A dermoscopic close-up of a skin lesion: 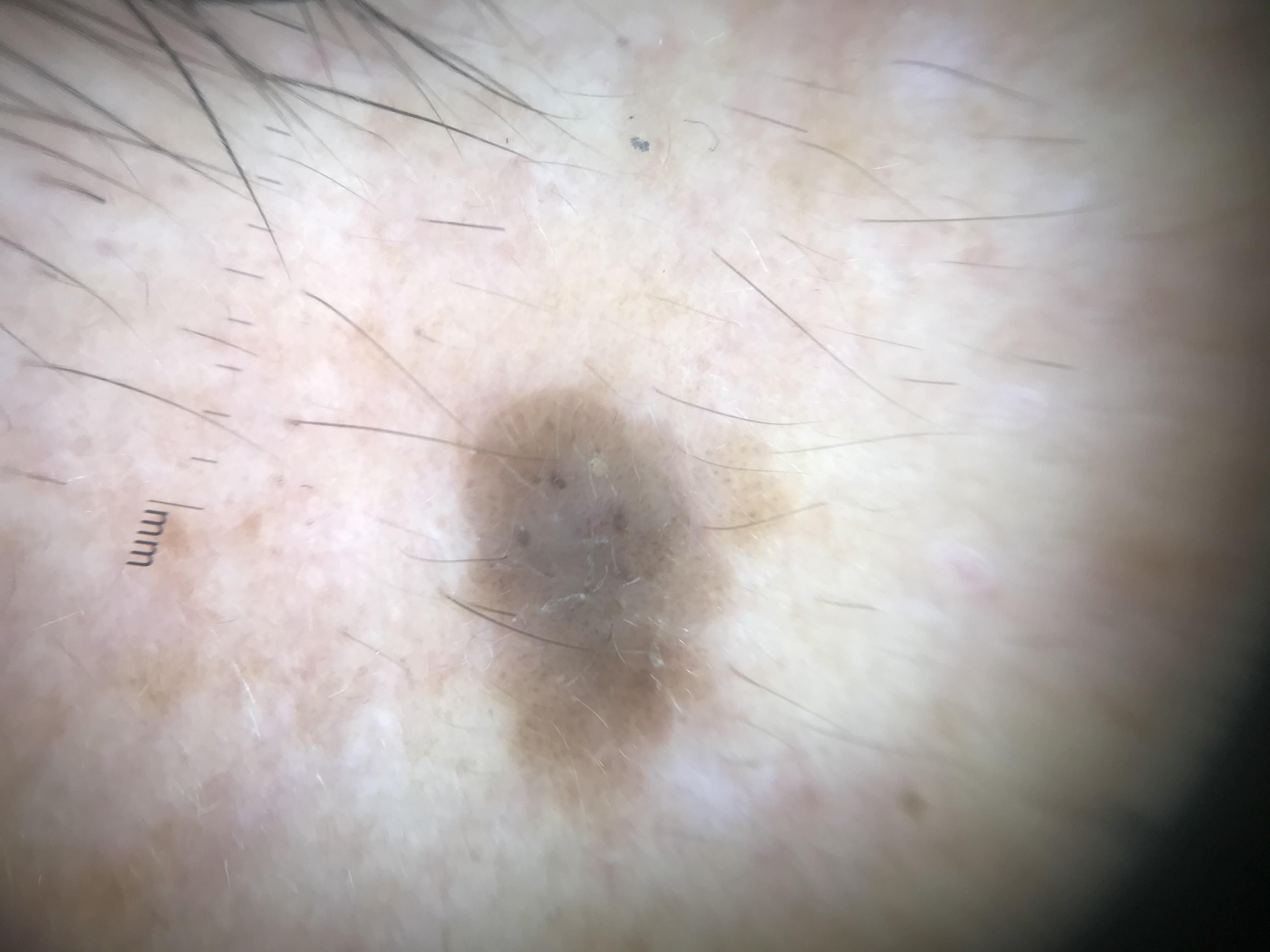The architecture is that of a keratinocytic lesion.
Labeled as a seborrheic keratosis.